A female patient age 55; a dermoscopy image of a skin lesion; acquired for a research image collection, with no referral diagnosis; a moderate number of moles by the patient's own estimate; the patient says their skin reddens painfully with sun exposure; by self-report, a prior organ transplant and immunosuppression — 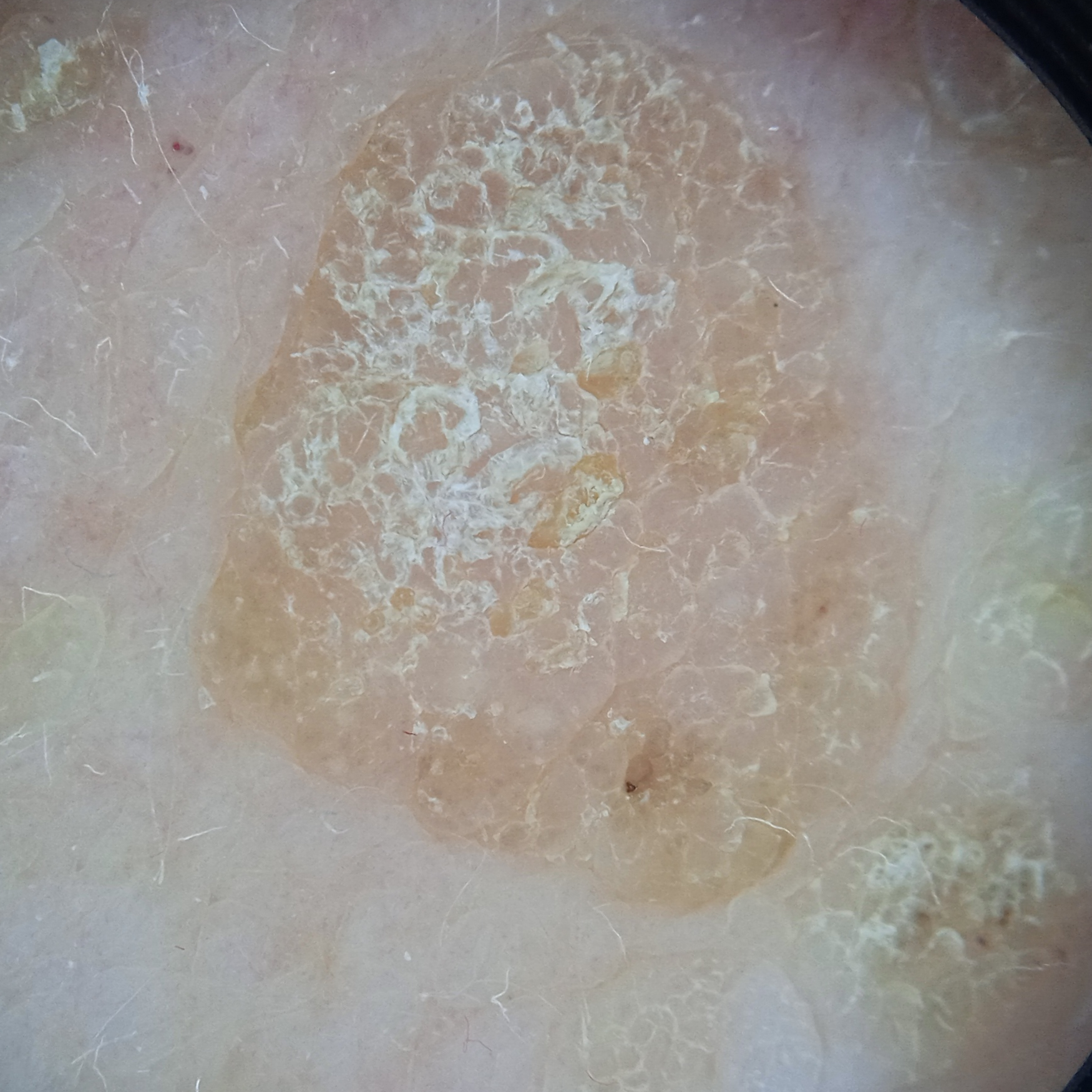location = the back; size = 10.6 mm; assessment = seborrheic keratosis (dermatologist consensus).